The lesion involves the arm, the patient is a female aged 30–39, this image was taken at a distance — 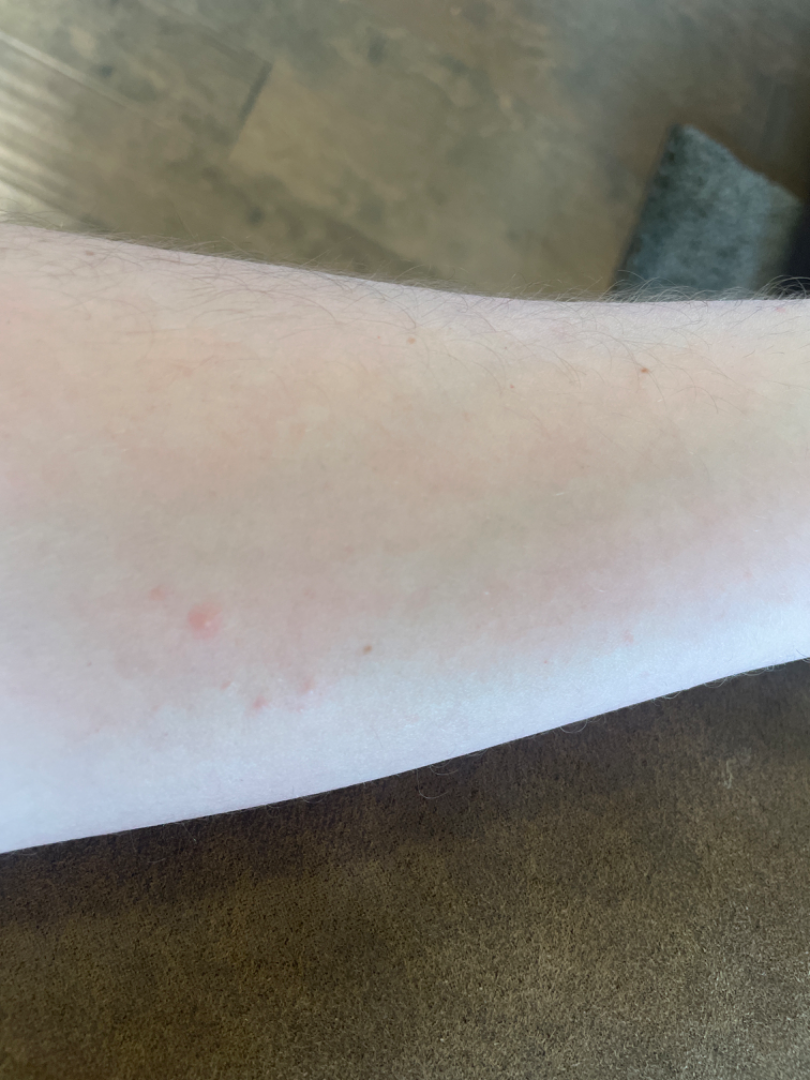Q: What is the lesion texture?
A: raised or bumpy
Q: Patient's own categorization?
A: skin that appeared healthy to them
Q: What symptoms does the patient report?
A: itching
Q: Duration?
A: about one day
Q: What is the dermatologist's impression?
A: most likely Insect Bite; with consideration of Allergic Contact Dermatitis; lower on the differential is Scabies